A male subject in their 60s; this is a dermoscopic photograph of a skin lesion:
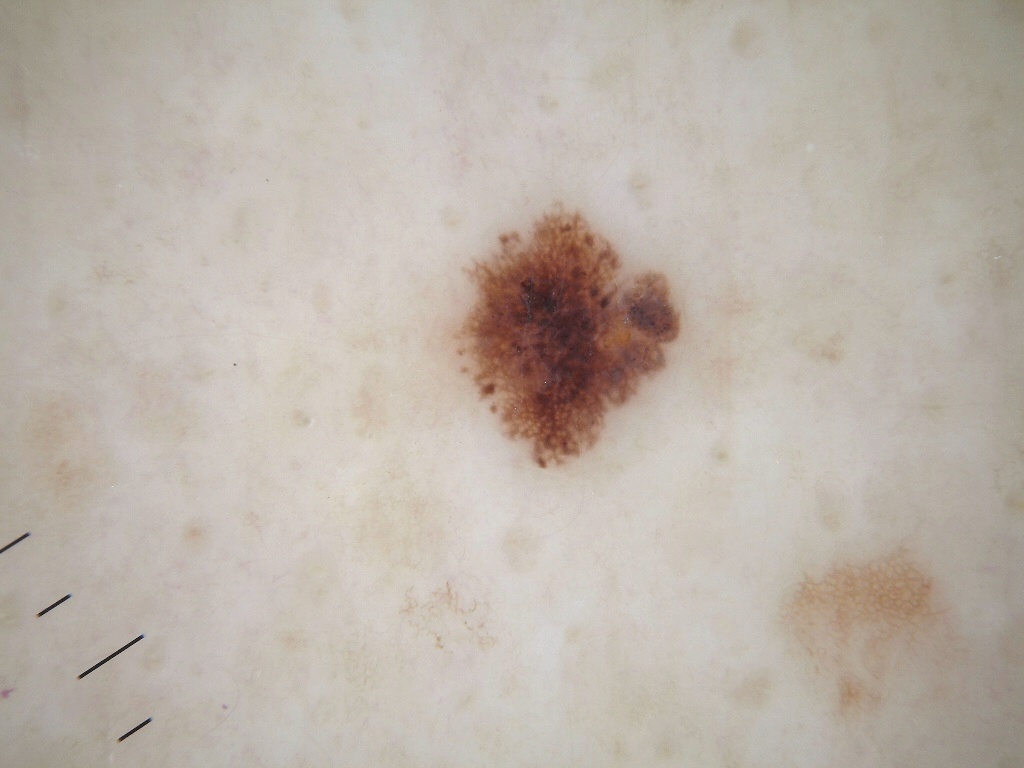• lesion extent — small
• lesion bbox — <box>438, 199, 707, 468</box>
• dermoscopic pattern — pigment network and globules; absent: negative network, milia-like cysts, and streaks
• assessment — a melanocytic nevus, a benign skin lesion